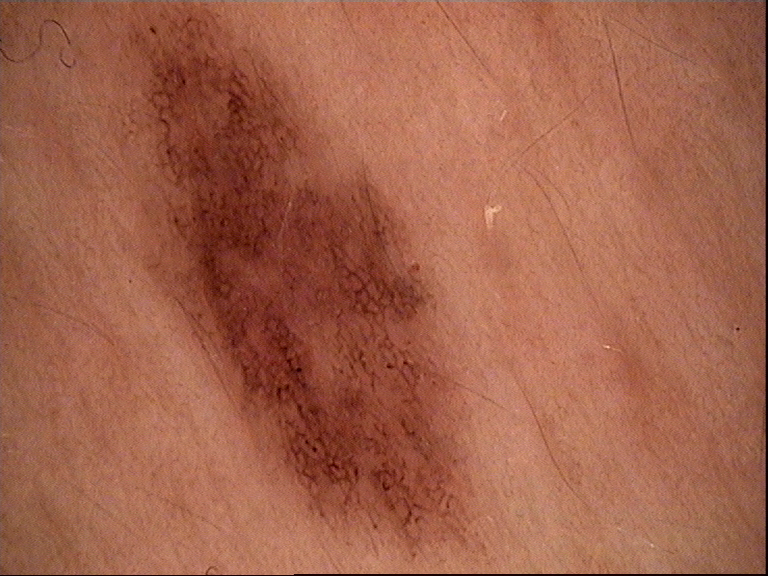{
  "diagnosis": {
    "name": "dysplastic junctional nevus",
    "code": "jd",
    "malignancy": "benign",
    "super_class": "melanocytic",
    "confirmation": "expert consensus"
  }
}